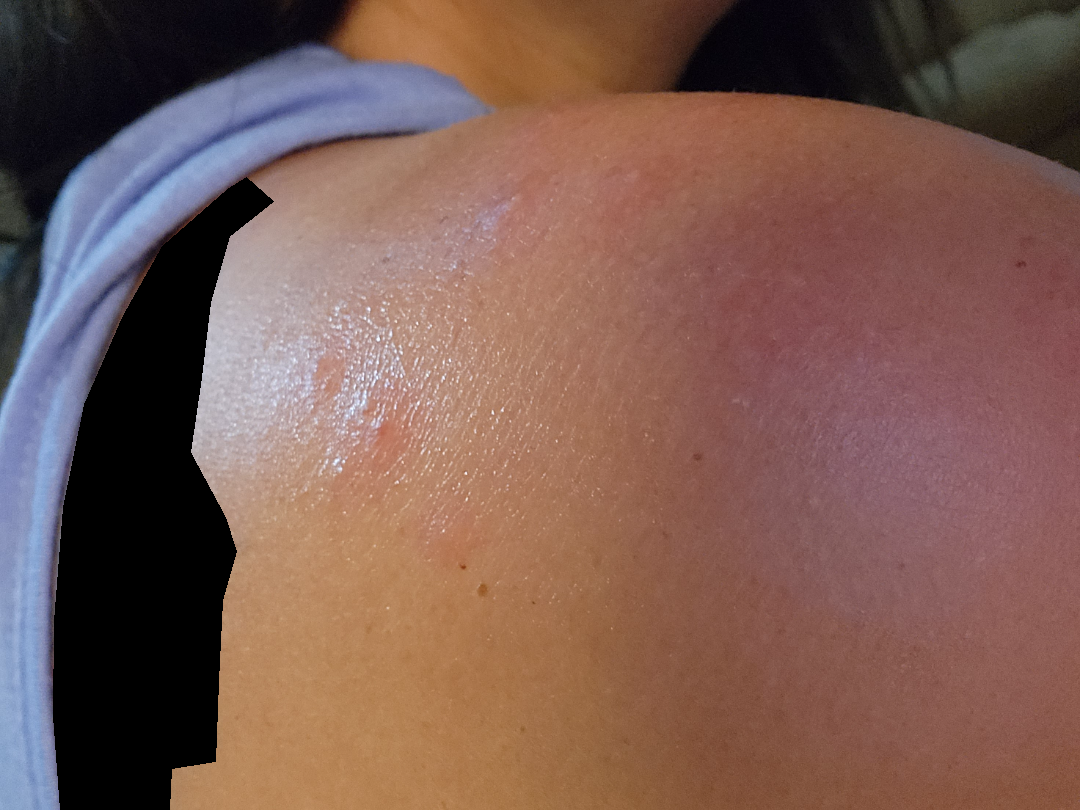The case was indeterminate on photographic review.